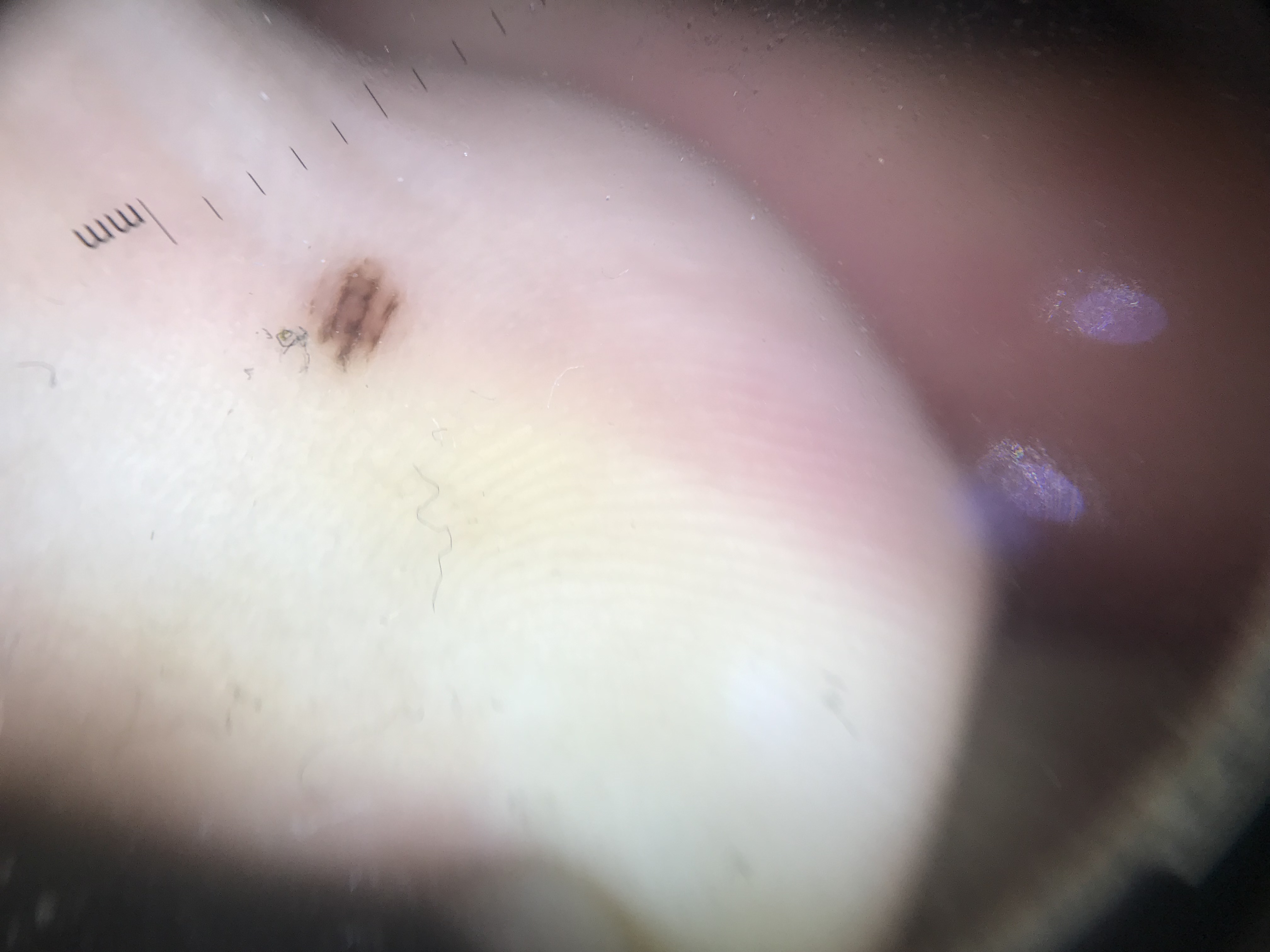A dermoscopic photograph of a skin lesion.
Diagnosed as an acral dysplastic junctional nevus.